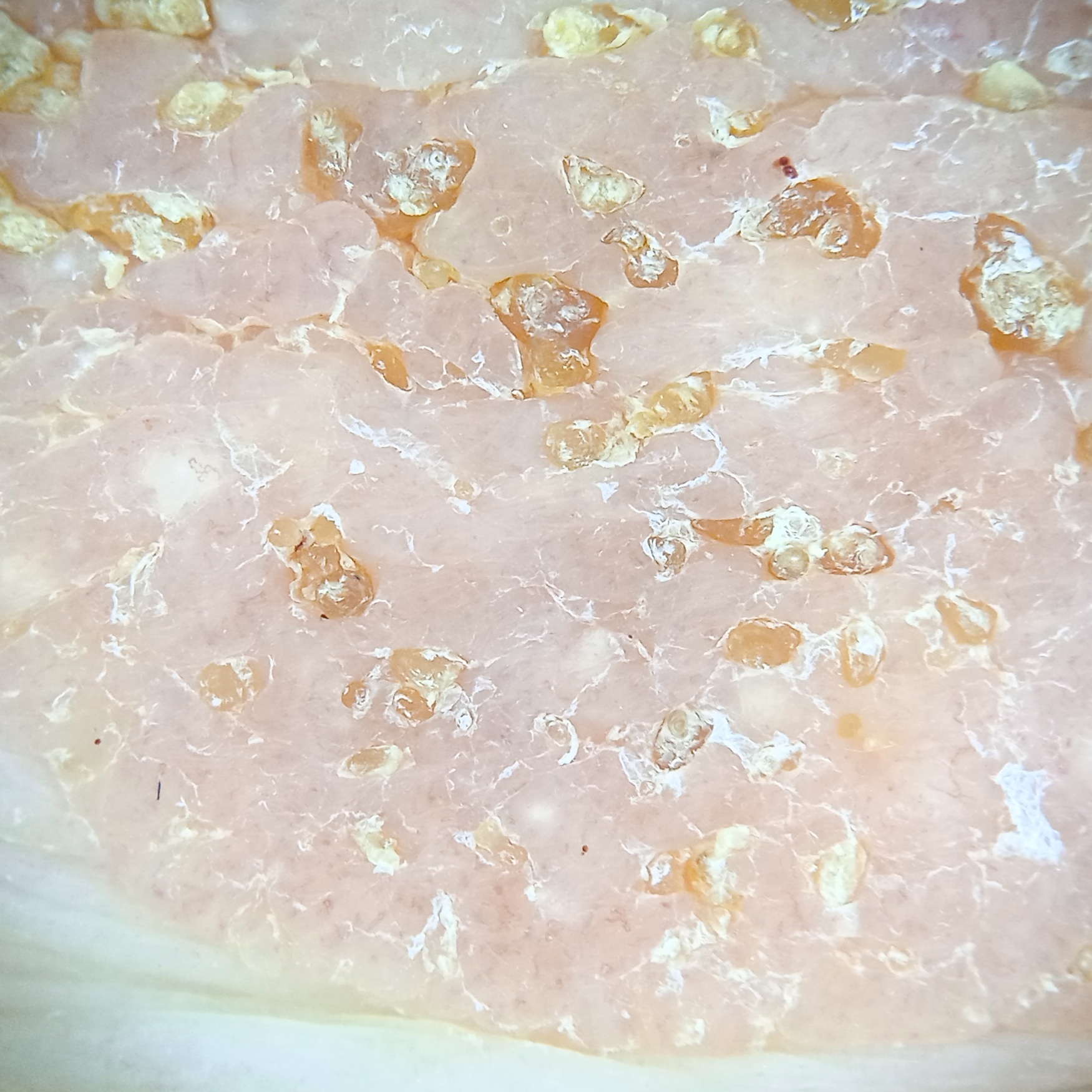Findings:
A dermatoscopic image of a skin lesion. A female patient 81 years of age. Located on the torso. Measuring roughly 31 mm.
Conclusion:
The lesion was assessed as a seborrheic keratosis.